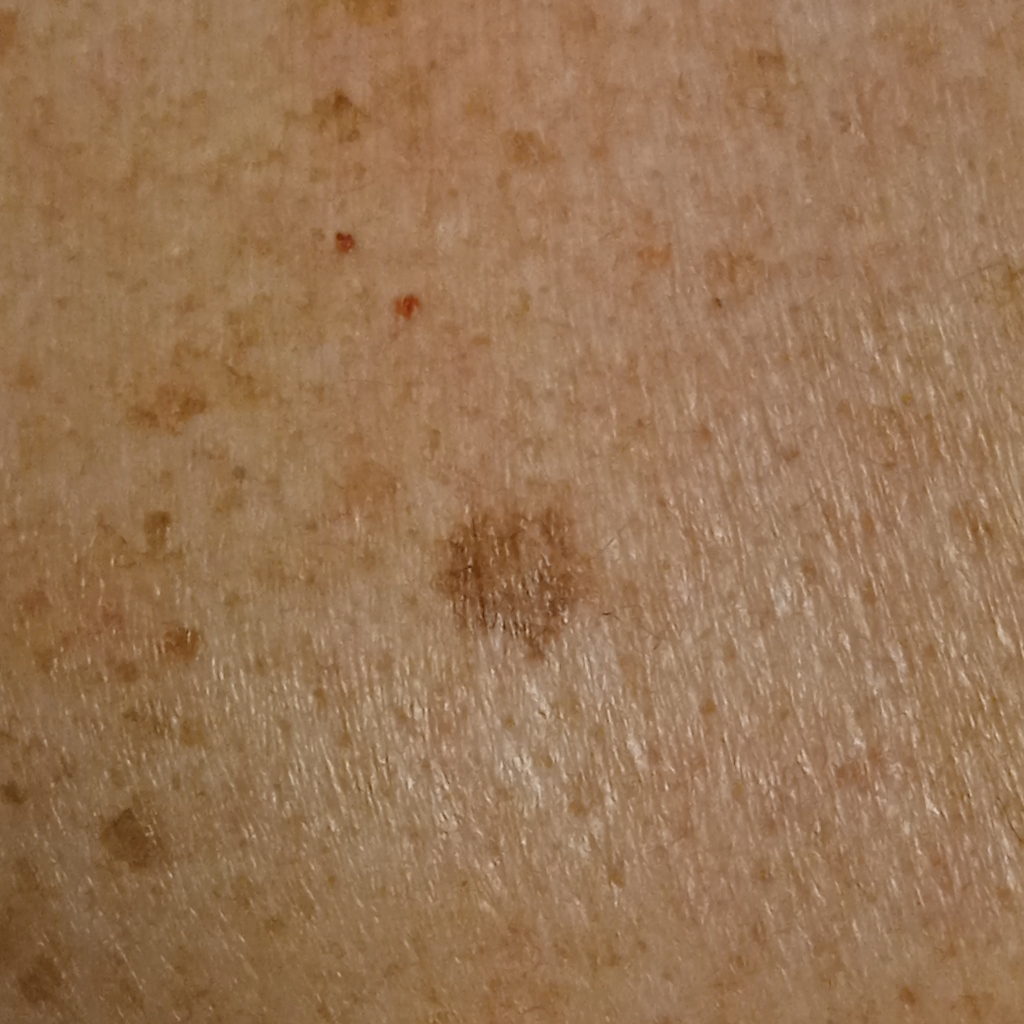The reviewing dermatologists could not reach a confident diagnosis. <case>
<patient>
<age>81</age>
<sex>male</sex>
</patient>
<referral>research study (no referral diagnosis)</referral>
<risk_factors>
<positive>a family history of skin cancer, a personal history of cancer</positive>
</risk_factors>
<sun_reaction>skin reddens with sun exposure</sun_reaction>
<image>clinical photograph</image>
<lesion_size>
<diameter_mm>8.0</diameter_mm>
</lesion_size>
</case>